A dermoscopy image of a single skin lesion:
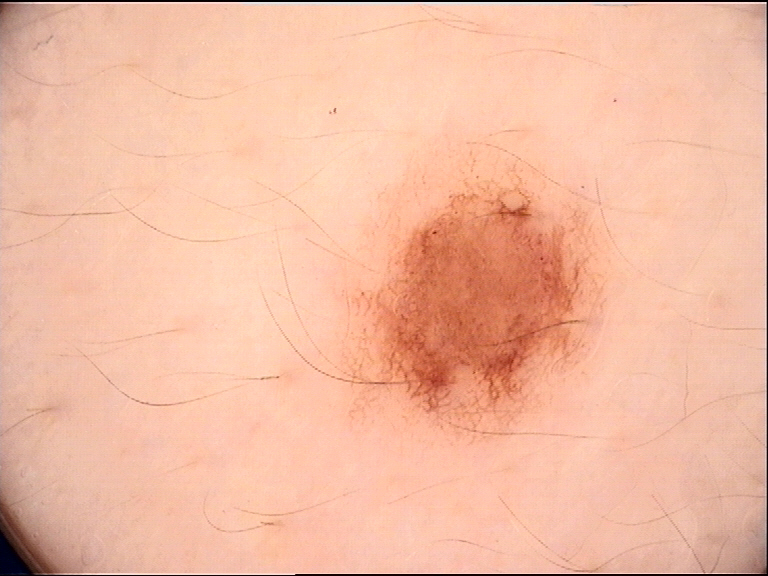Conclusion:
Diagnosed as a benign lesion — a dysplastic junctional nevus.